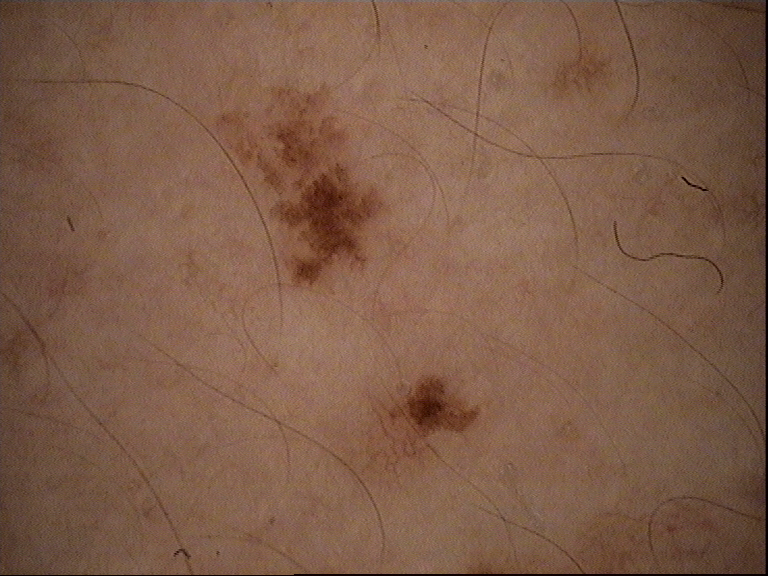• image type · dermoscopy
• diagnosis · dysplastic junctional nevus (expert consensus)